The subject is a male aged 23-27. Dermoscopy of a skin lesion — 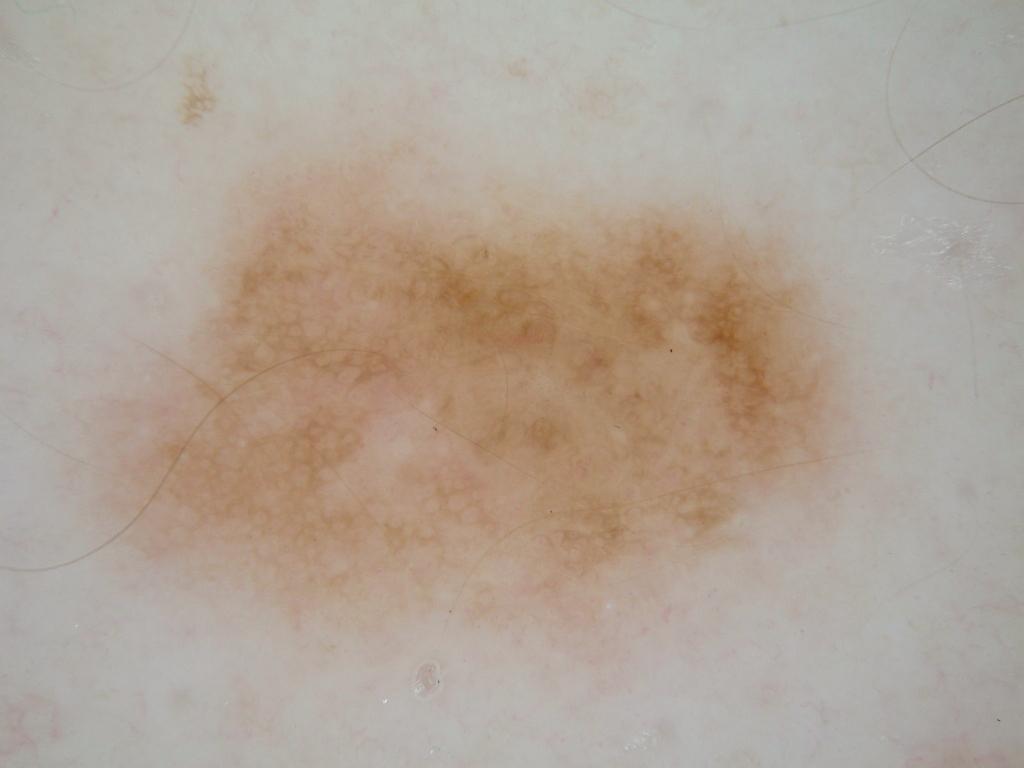dermoscopic pattern — pigment network; absent: streaks, globules, negative network, and milia-like cysts | lesion bbox — 60 135 867 702 | diagnosis — a melanocytic nevus, a benign lesion.